A dermoscopy image of a single skin lesion.
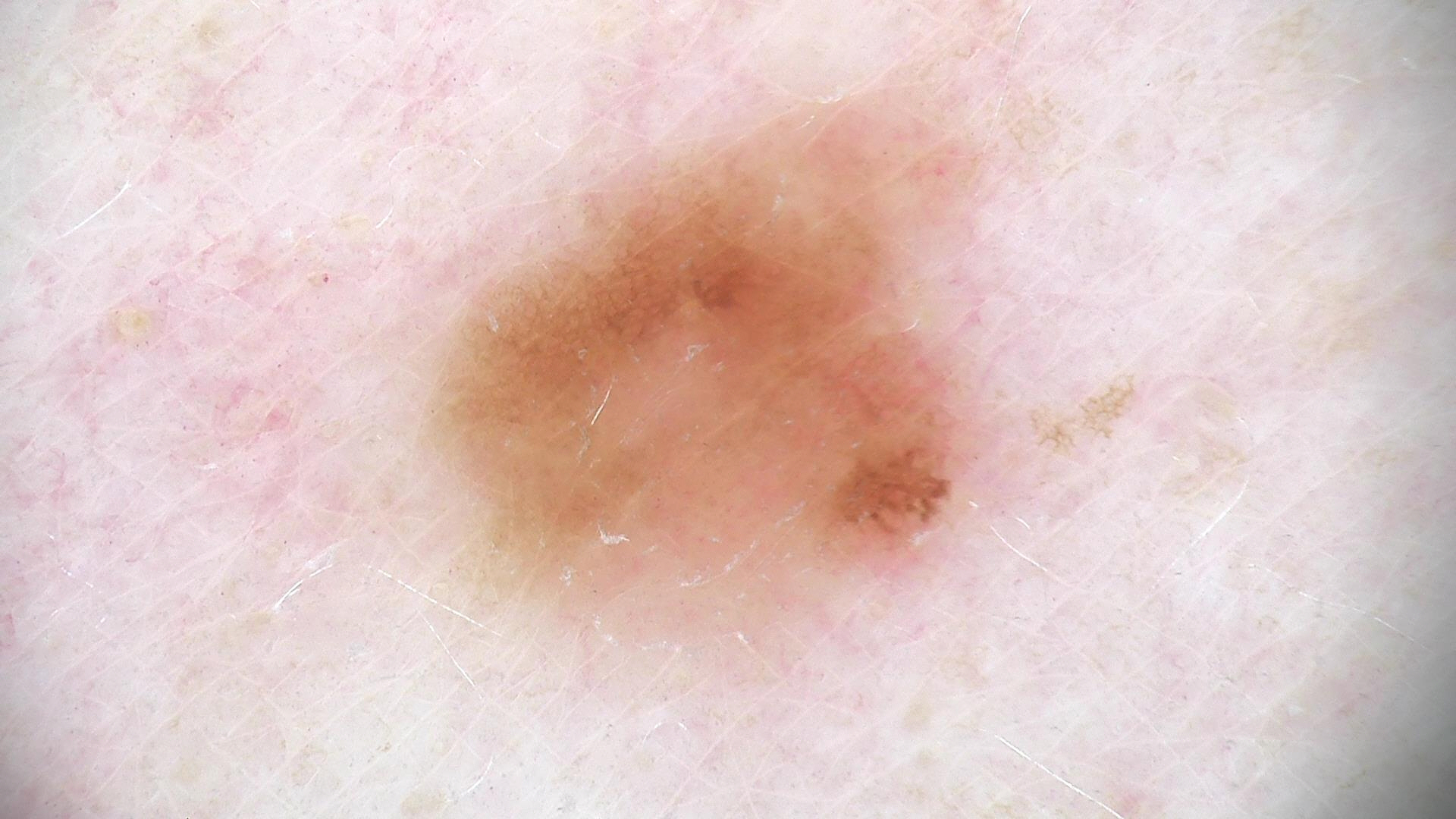Conclusion: Diagnosed as a dysplastic junctional nevus.